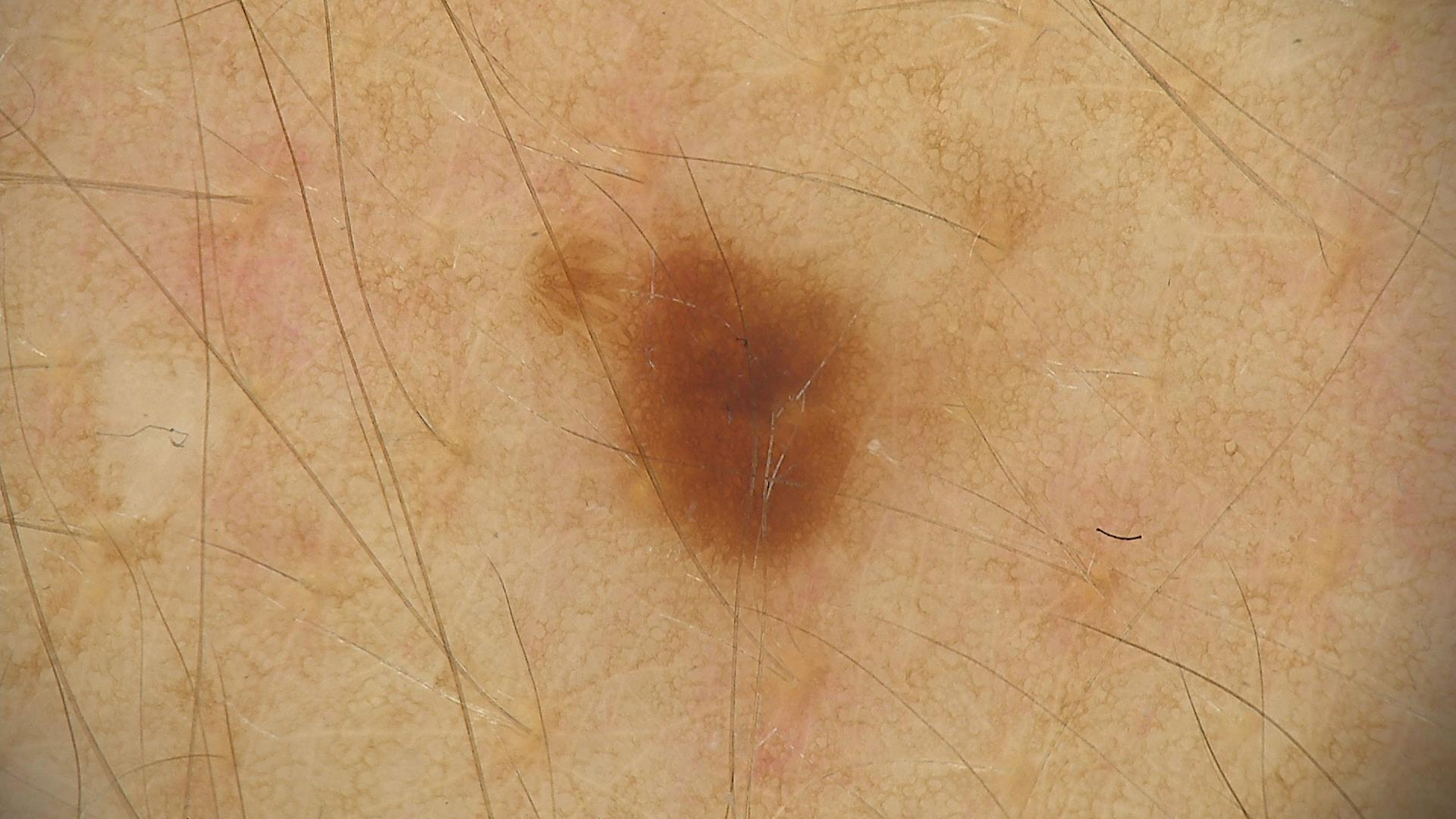Impression:
Labeled as a benign lesion — a dysplastic junctional nevus.